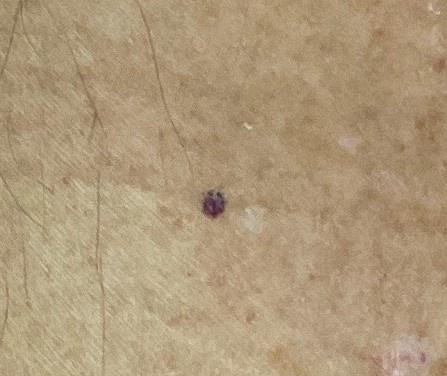melanoma history = melanoma in a first-degree relative | modality = clinical photo (overview) | subject = male, aged around 70 | body site = a lower extremity | impression = vascular lesion.